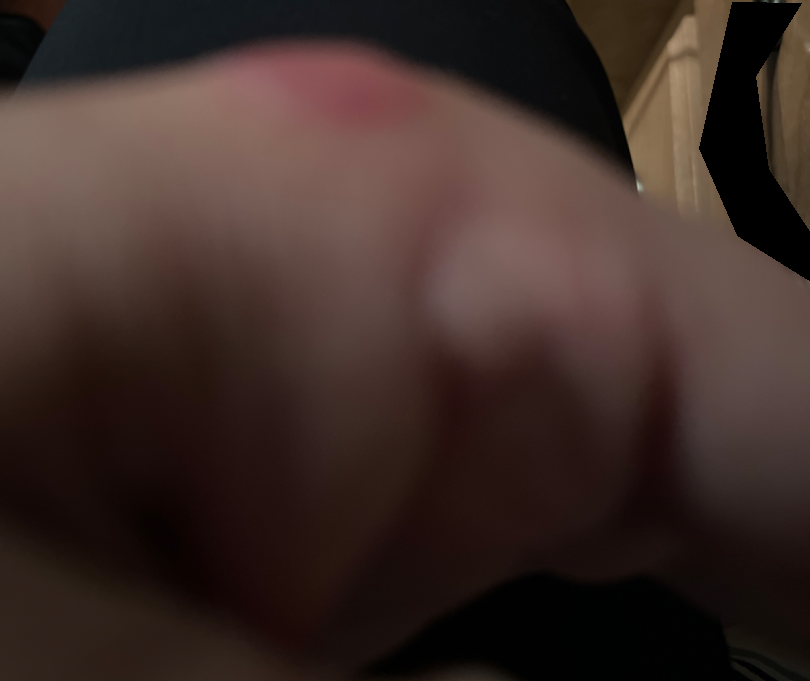The image was not sufficient for the reviewer to characterize the skin condition.
This image was taken at an angle.
The affected area is the back of the hand.
The contributor is 50–59, female.